The photograph is a close-up of the affected area.
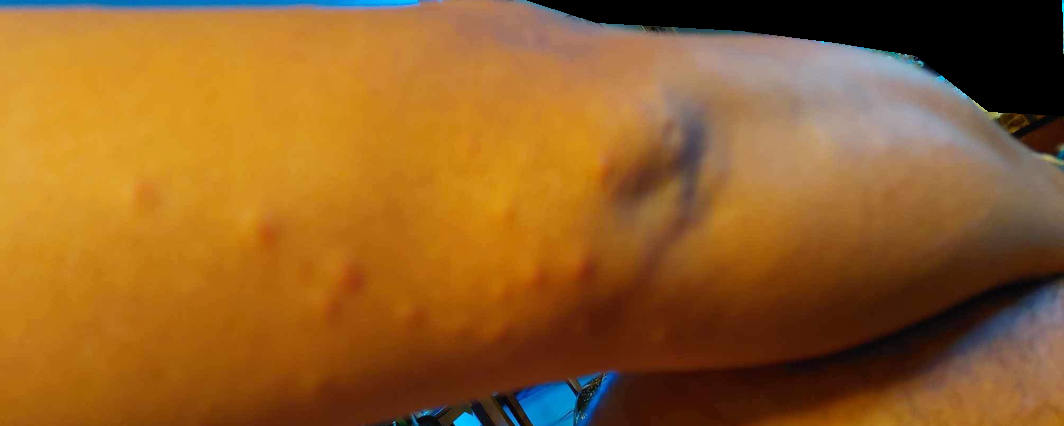On dermatologist assessment of the image, the impression on review was Insect Bite.